A dermoscopic photograph of a skin lesion.
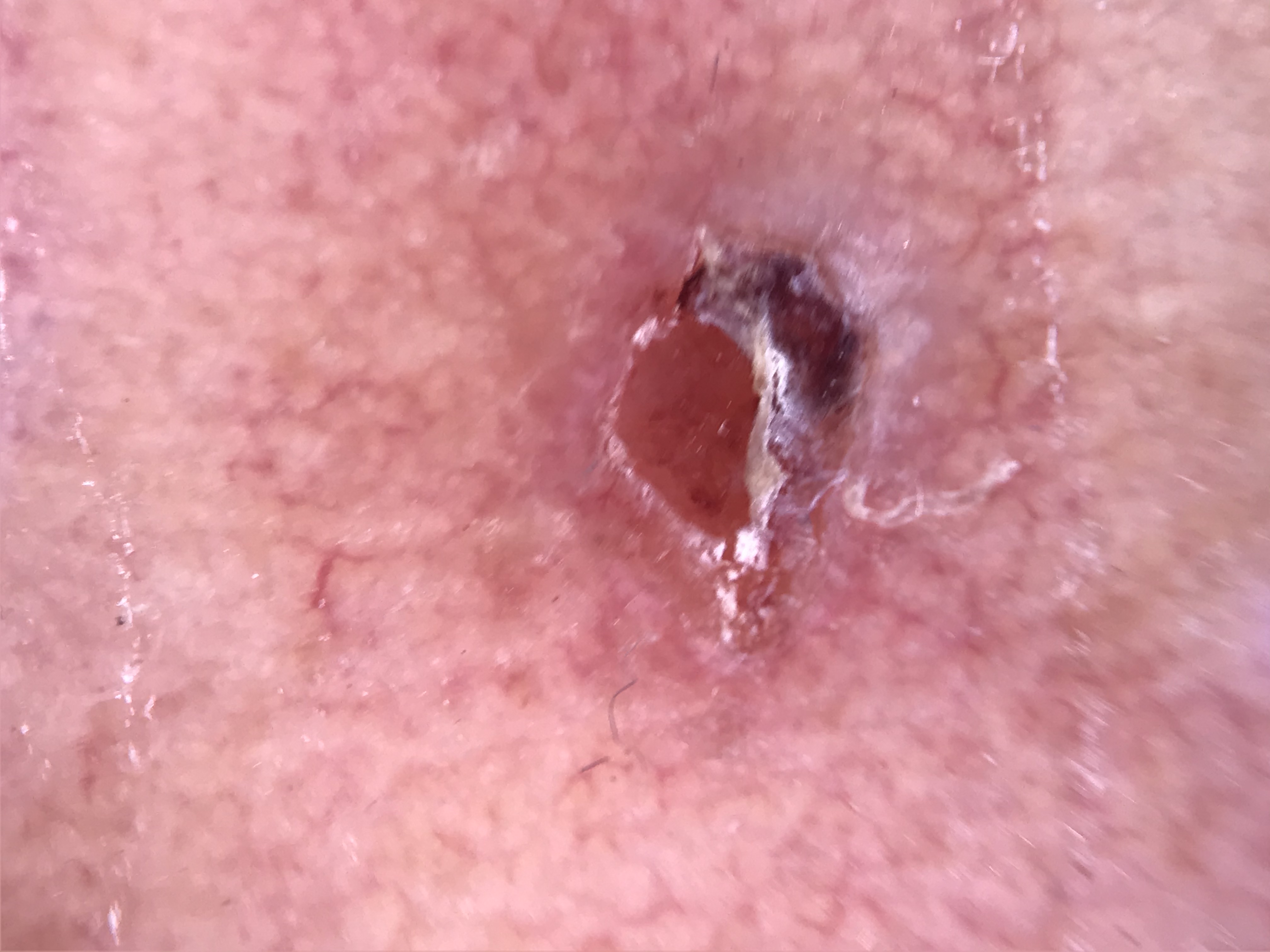Case:
– pathology: squamous cell carcinoma (biopsy-proven)